Dermoscopy of a skin lesion, a male patient aged approximately 35 — 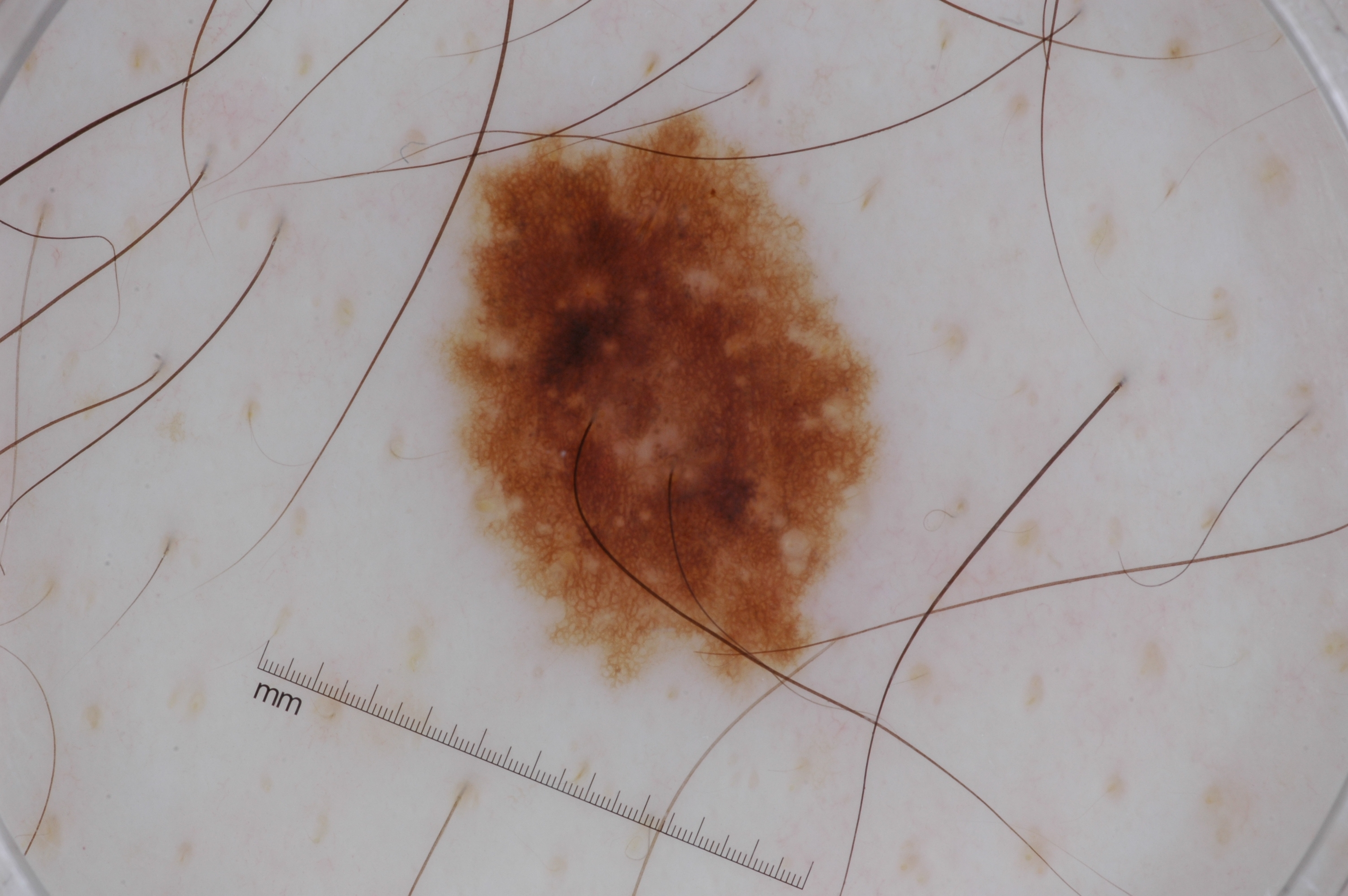Notes:
- dermoscopic pattern · pigment network and milia-like cysts; absent: negative network and streaks
- bounding box · [453, 126, 874, 672]
- diagnosis · a melanocytic nevus, a benign lesion